Located on the leg · this image was taken at an angle: 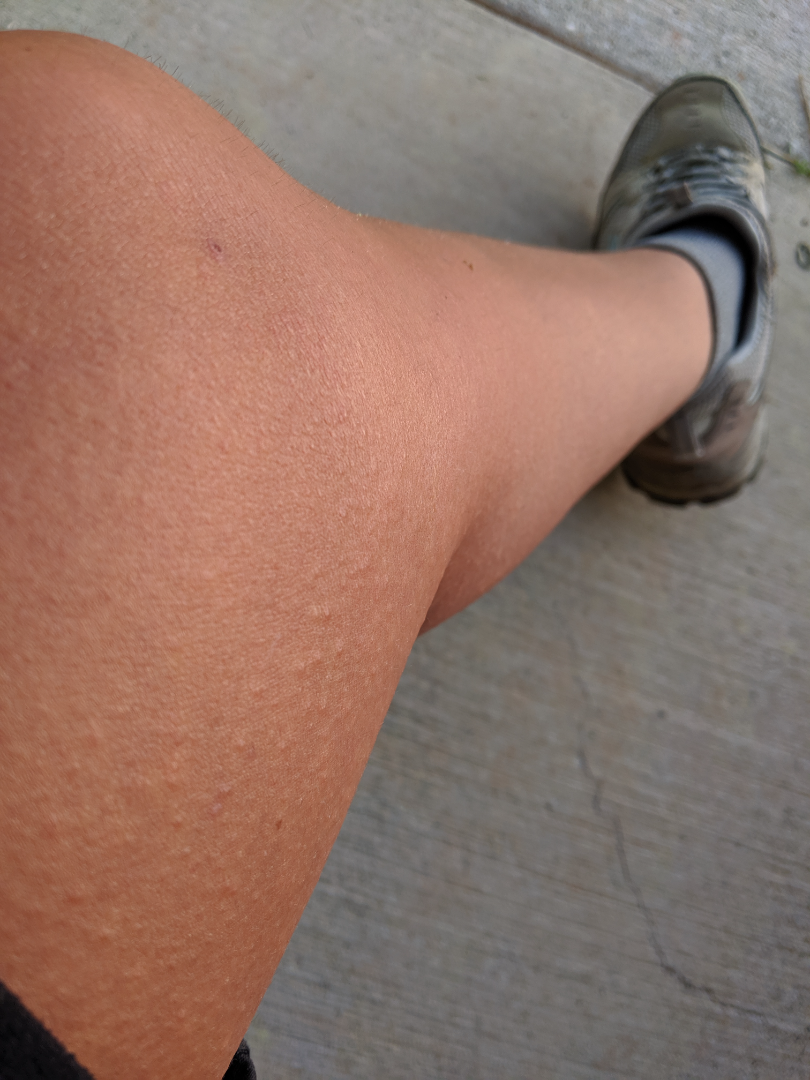The skin findings could not be characterized from the image. The patient reports the condition has been present for about one day. Symptoms reported: itching. Fitzpatrick skin type IV. Texture is reported as raised or bumpy. Self-categorized by the patient as a rash.